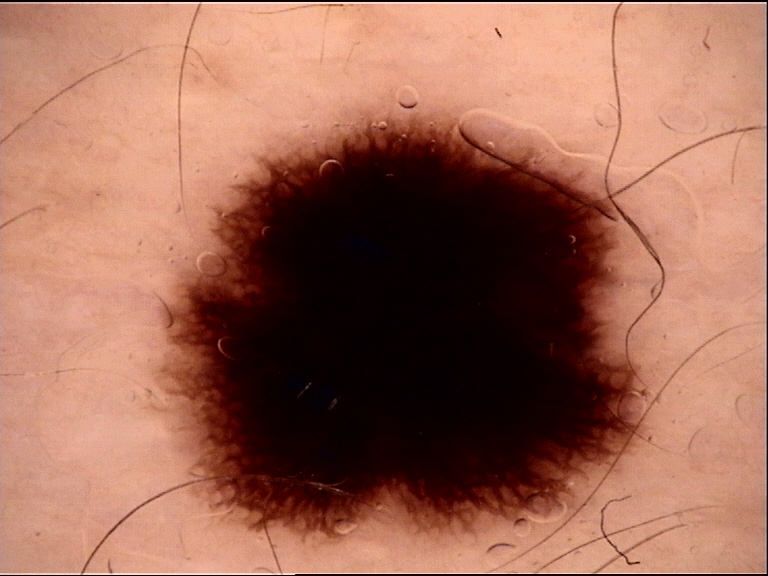lesion type: dysplastic, junctional | assessment: Spitz/Reed nevus (expert consensus).